Skin tone: FST III; lay graders estimated 2 on the Monk Skin Tone · the patient reported no systemic symptoms · the patient indicates darkening · the affected area is the back of the hand · this is a close-up image · the condition has been present for three to twelve months:
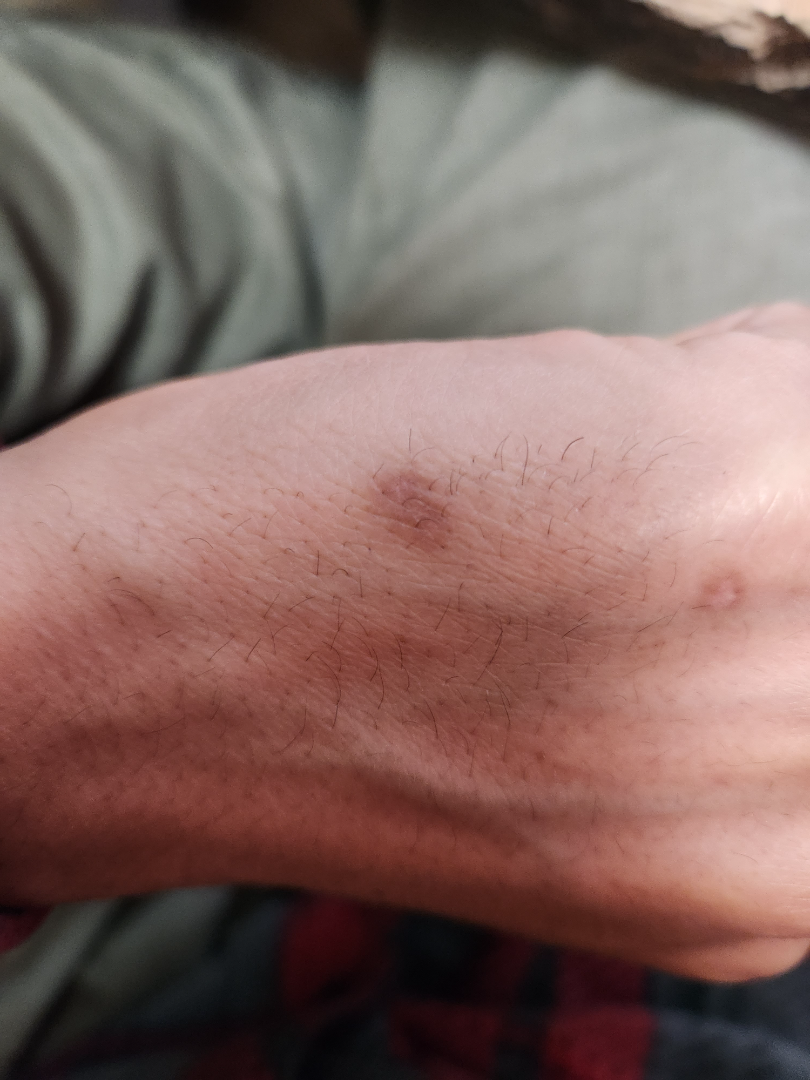impression = the leading consideration is Prurigo nodularis; also raised was Lichen planus/lichenoid eruption; also consider Post-Inflammatory hyperpigmentation; less likely is Eczema.